The photograph is a close-up of the affected area; the lesion involves the arm; the subject is male:
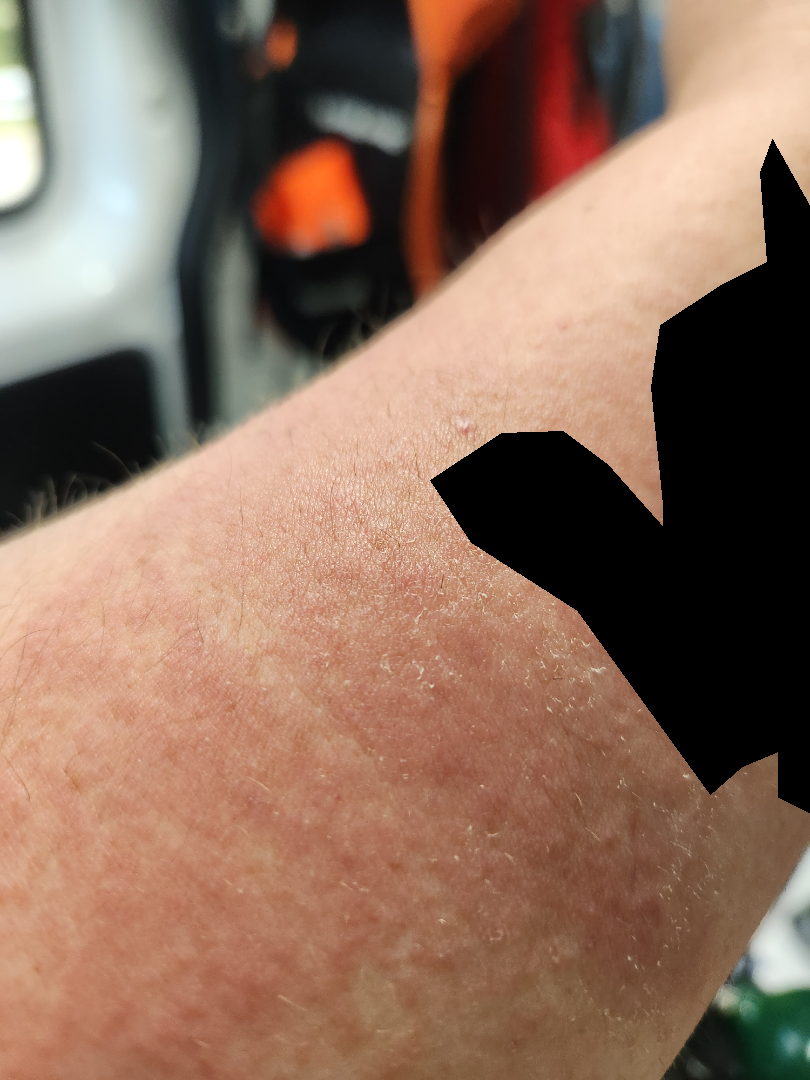| field | value |
|---|---|
| self-categorized as | a rash |
| texture | rough or flaky and raised or bumpy |
| duration | less than one week |
| reported symptoms | enlargement and itching |
| differential diagnosis | Lichenified eczematous dermatitis (most likely); Allergic Contact Dermatitis (considered) |